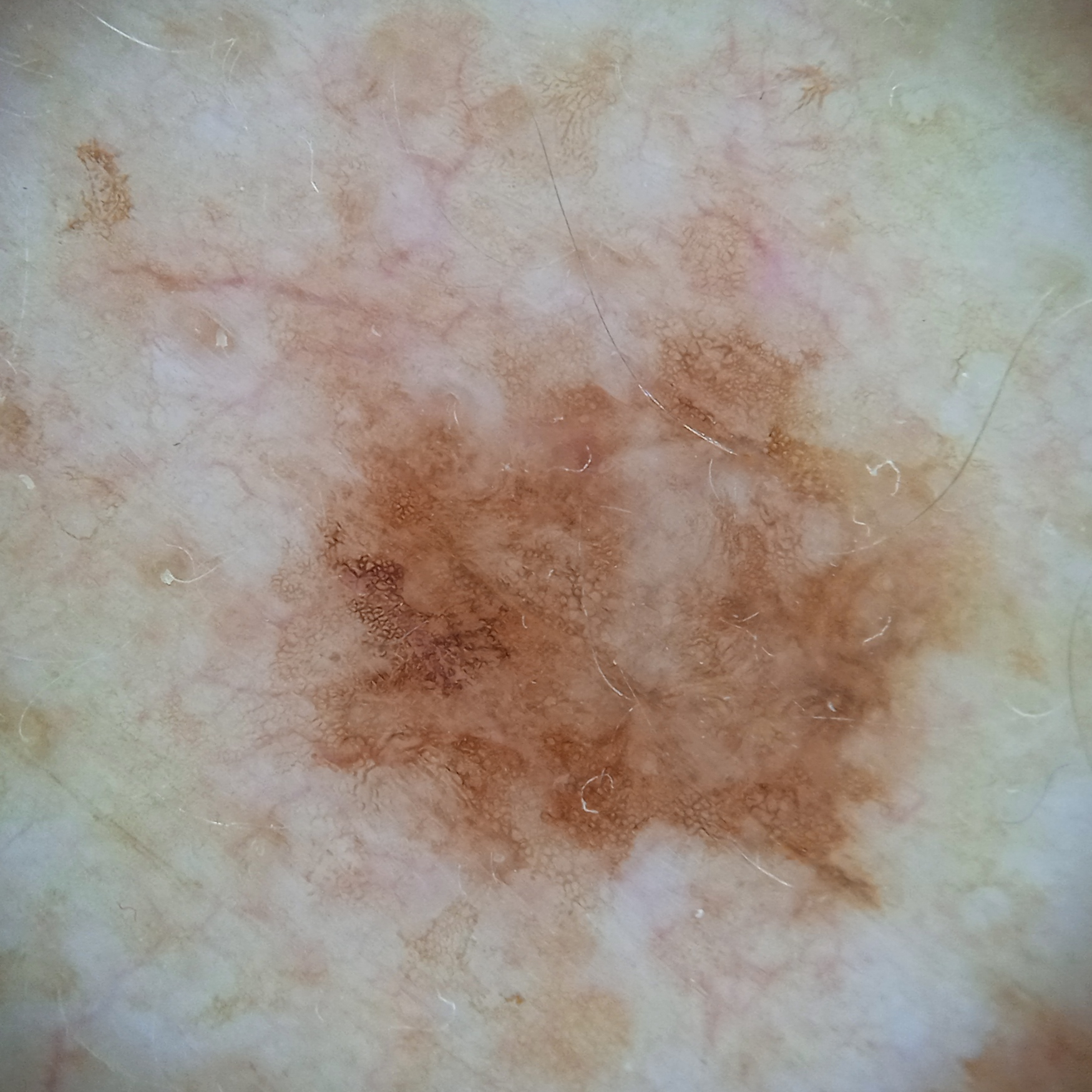The reviewing dermatologists could not reach a confident diagnosis. A male patient 81 years old. Acquired for a research image collection, with no referral diagnosis. A skin lesion imaged with a dermatoscope. The lesion measures approximately 8 mm.